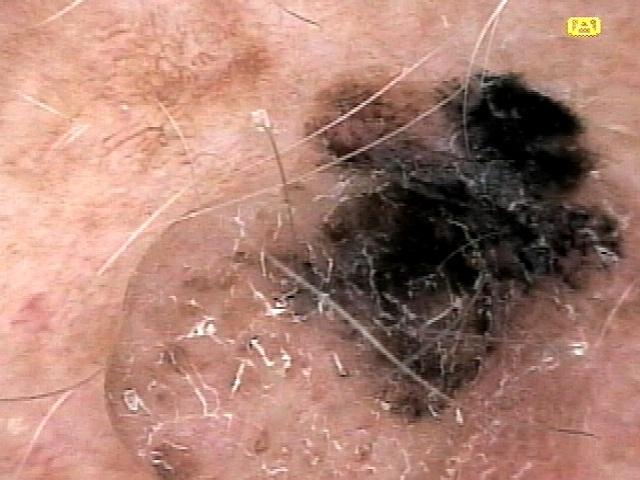<record>
<diagnosis>
<name>Melanoma</name>
<malignancy>malignant</malignancy>
<confirmation>histopathology</confirmation>
</diagnosis>
</record>